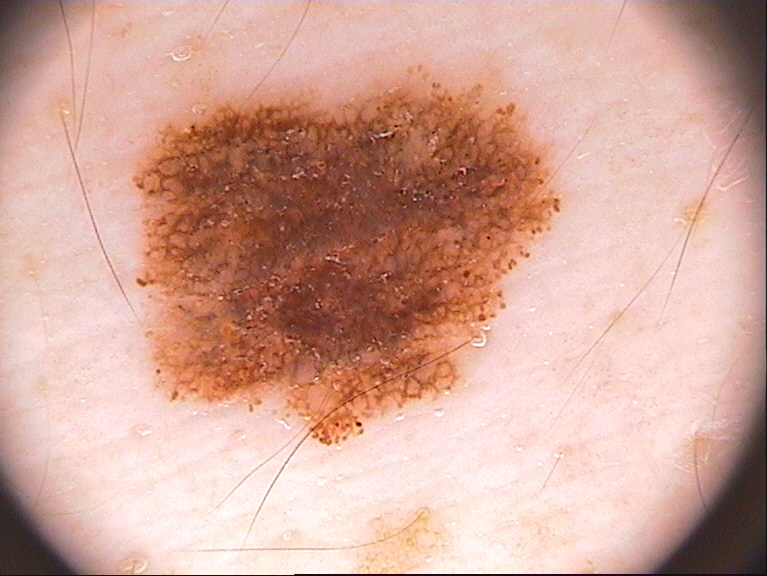Case summary:
* image type · dermoscopy of a skin lesion
* patient · male, in their 50s
* extent · moderate
* dermoscopic findings · pigment network and globules; absent: negative network, milia-like cysts, and streaks
* lesion location · (132, 62, 563, 447)
* assessment · a melanocytic nevus, a benign lesion